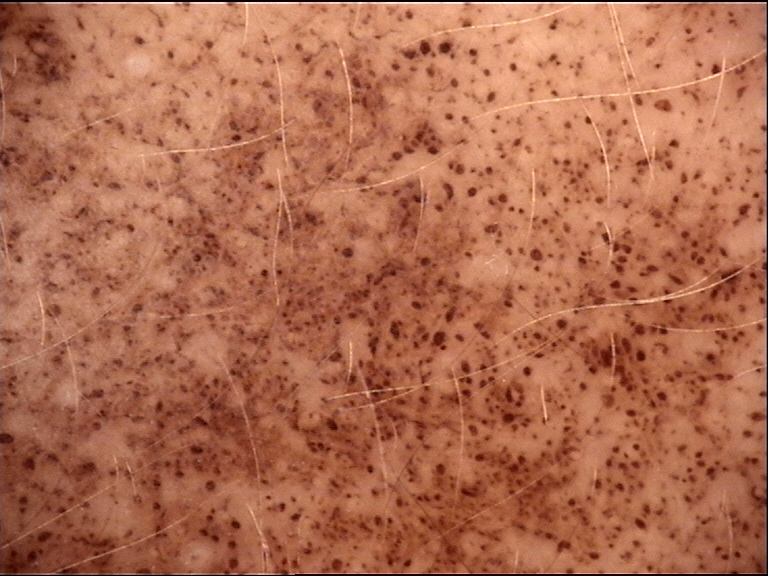Conclusion: The diagnosis was a congenital junctional nevus.